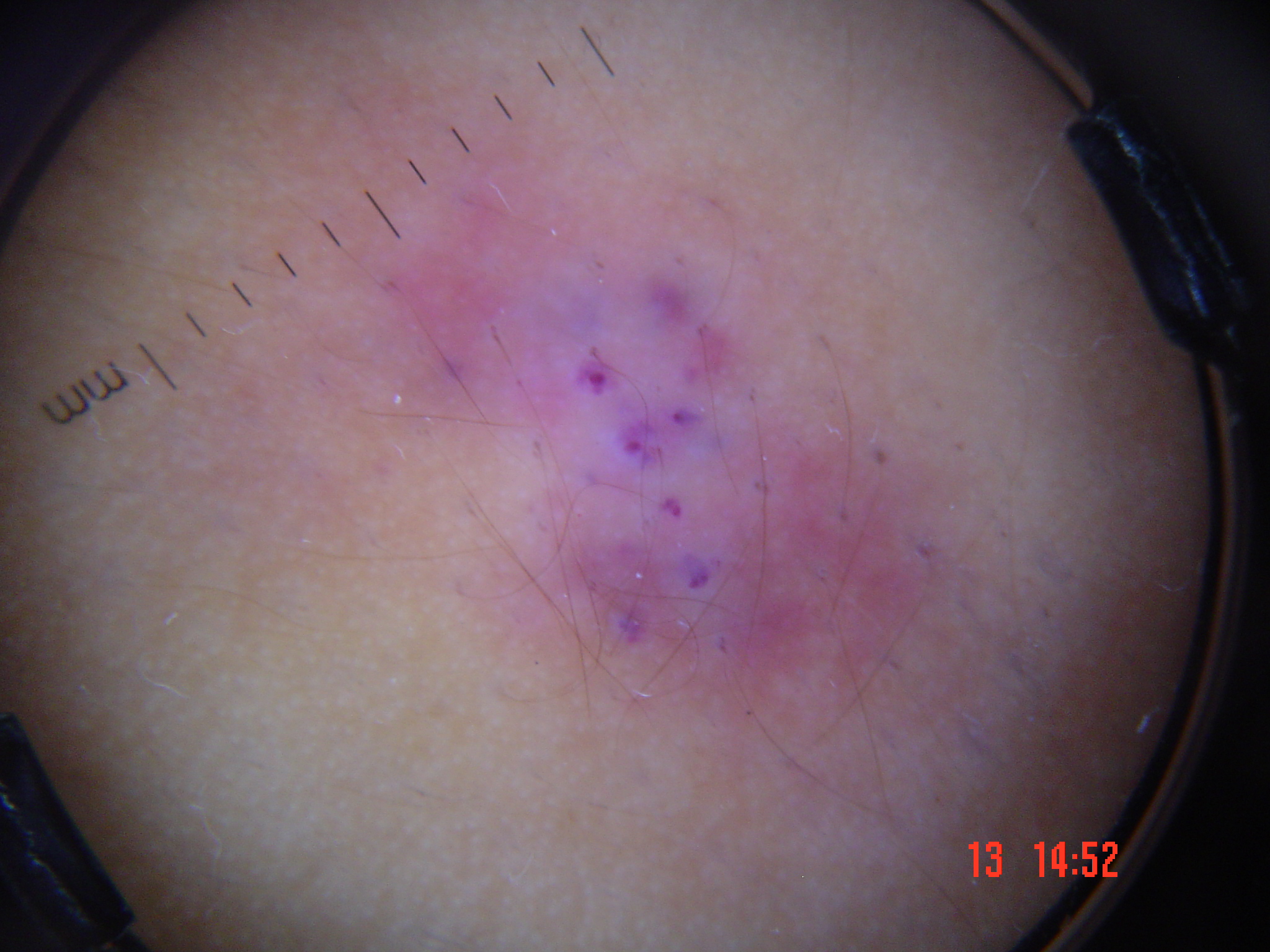A dermatoscopic image of a skin lesion.
This is a vascular lesion.
Classified as a benign lesion — an angiokeratoma.